The photograph is a close-up of the affected area: 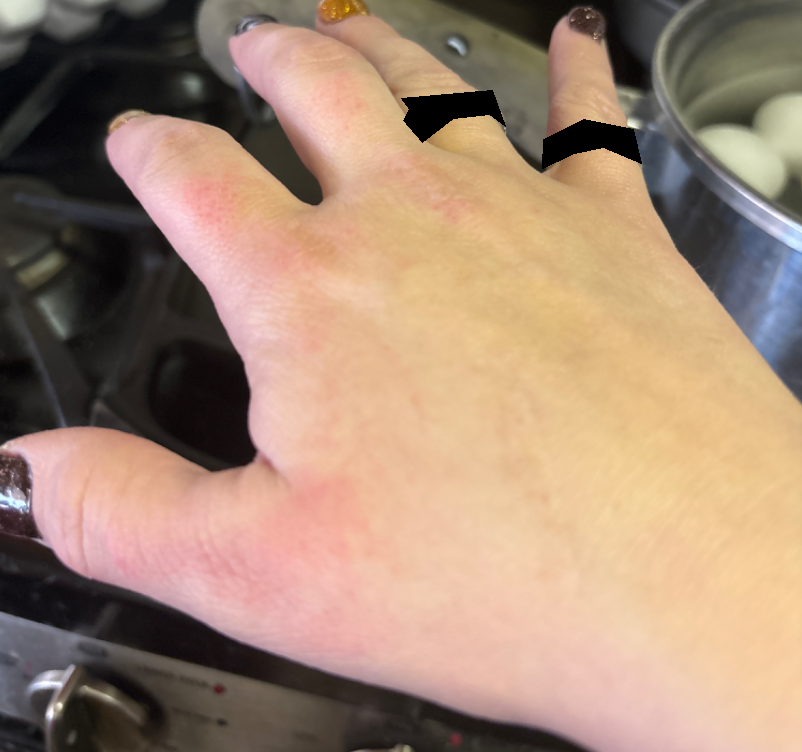On remote dermatologist review, most consistent with Eczema.